A dermoscopic photograph of a skin lesion:
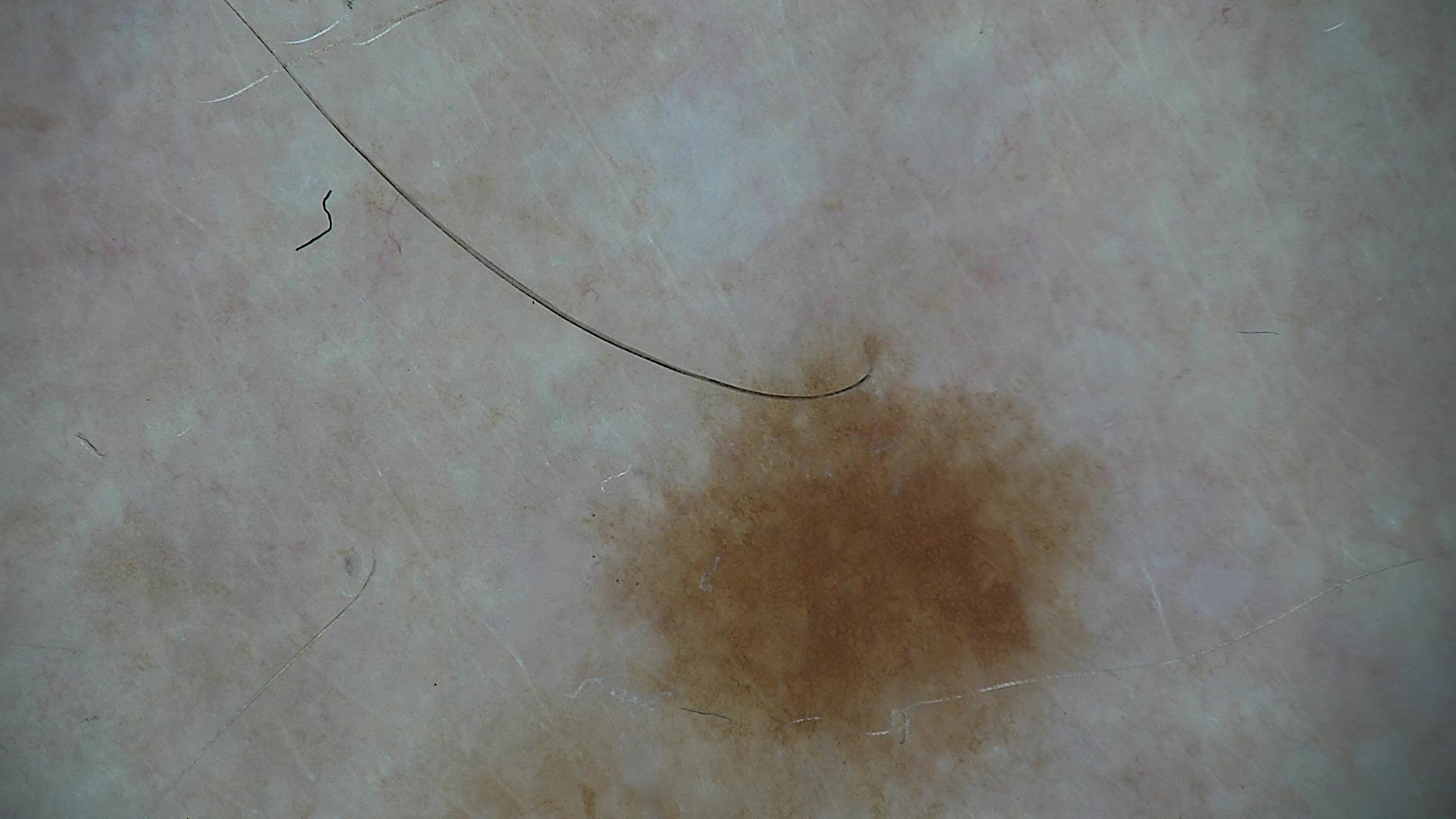diagnosis:
  name: dysplastic junctional nevus
  code: jd
  malignancy: benign
  super_class: melanocytic
  confirmation: expert consensus